Texture is reported as flat · self-categorized by the patient as a rash · reported duration is about one day · the patient indicates itching · located on the leg · no constitutional symptoms were reported · the photo was captured at an angle — 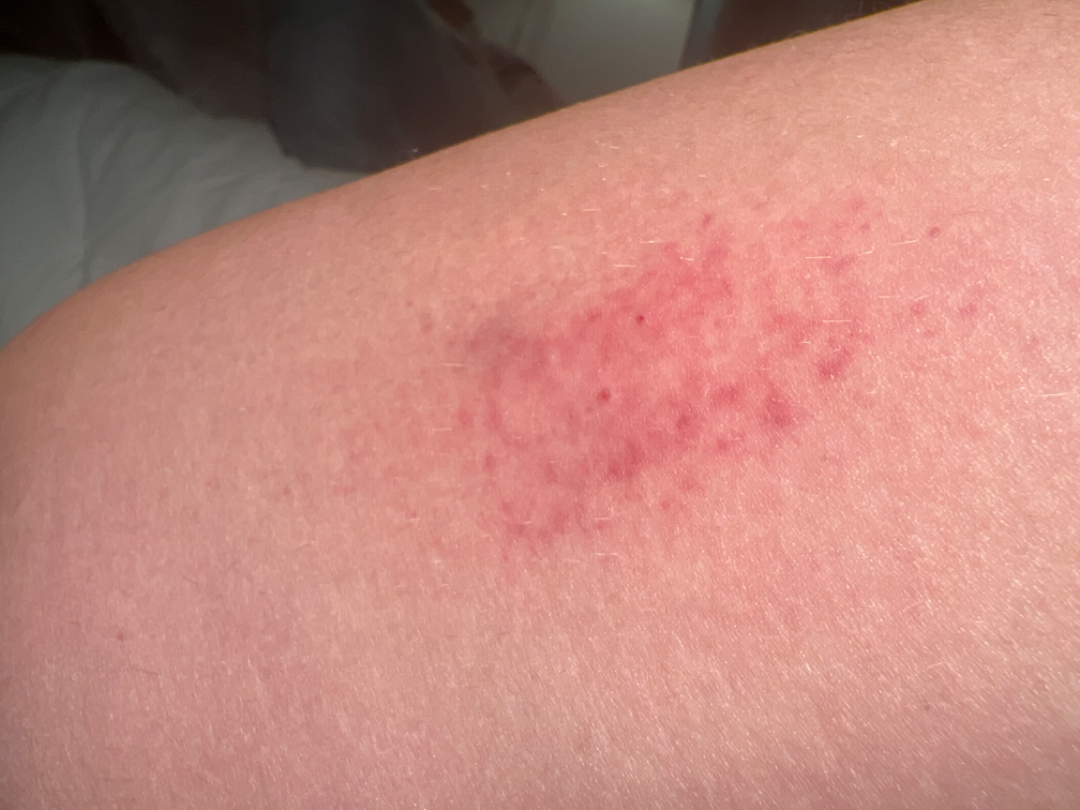The skin condition could not be confidently assessed from this image.